Fitzpatrick phototype II · reported lesion symptoms include itching, darkening, burning, bothersome appearance, enlargement and pain · the contributor is 30–39, female · located on the head or neck, top or side of the foot, arm, back of the hand and leg · the patient indicates the condition has been present for one to three months · the patient considered this a rash · the patient indicates the lesion is fluid-filled and raised or bumpy · the photograph was taken at a distance: 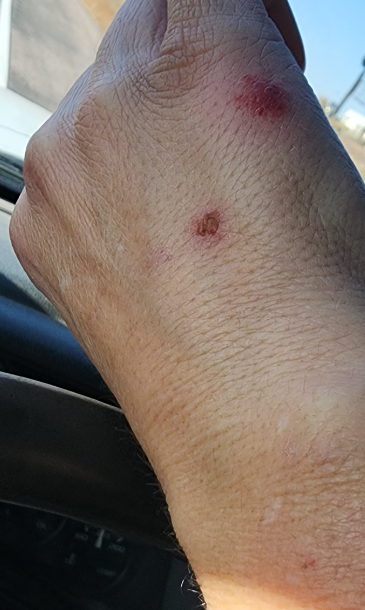• assessment · ungradable on photographic review